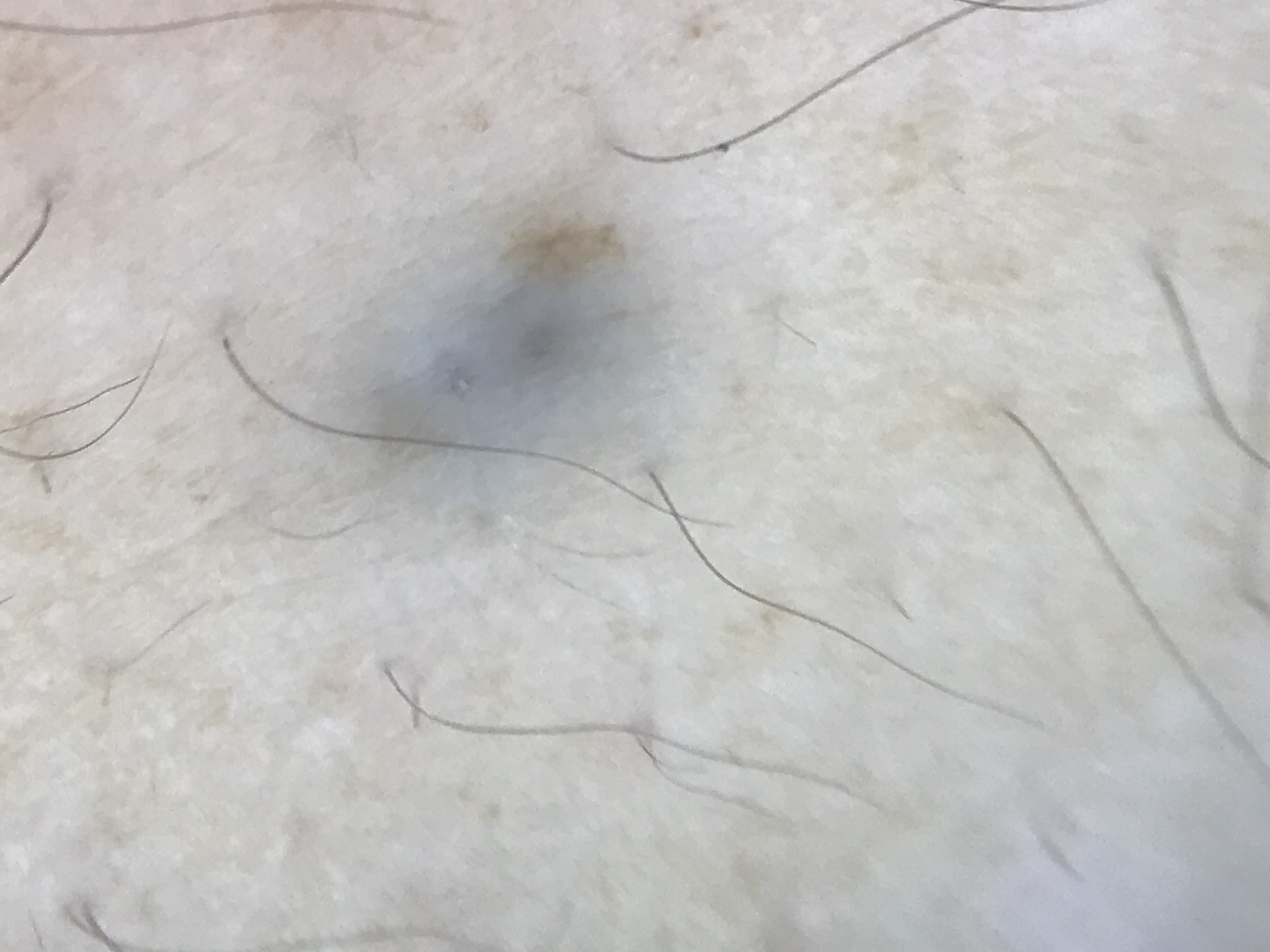Summary:
A dermoscopic photograph of a skin lesion.
Conclusion:
Diagnosed as a banal lesion — a blue nevus.